The patient notes itching. A close-up photograph. Texture is reported as fluid-filled. No associated systemic symptoms reported. FST I. The patient is 40–49, male. Located on the leg. The condition has been present for about one day. The patient described the issue as a rash:
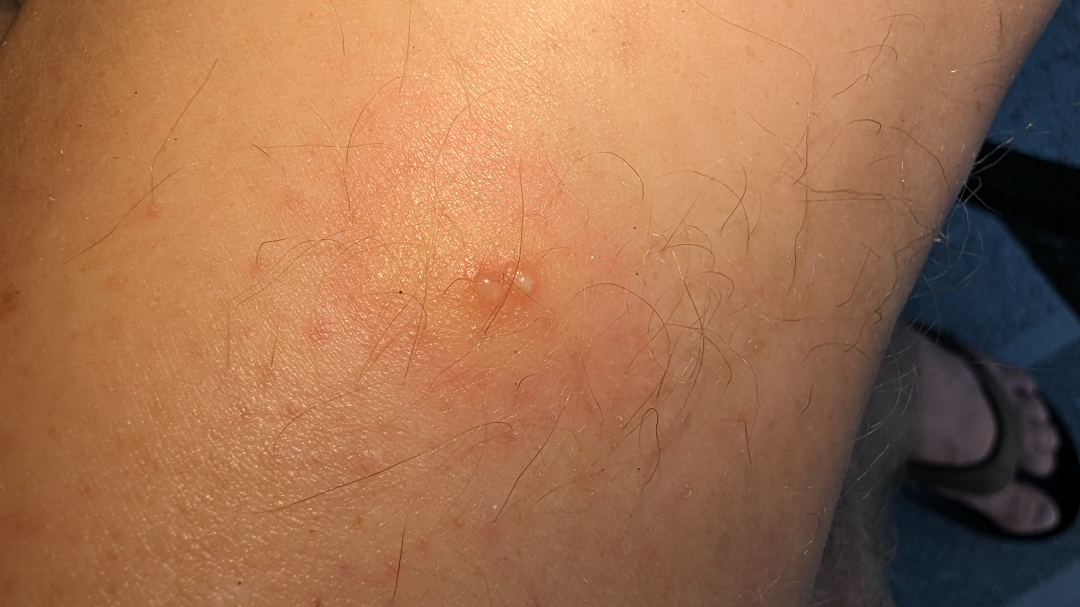The primary impression is Insect Bite; less probable is Erythema migrans; a more distant consideration is Impetigo; less likely is Drug Rash; lower on the differential is Allergic Contact Dermatitis; a remote consideration is Abscess.